This image was taken at an angle; the lesion involves the leg: 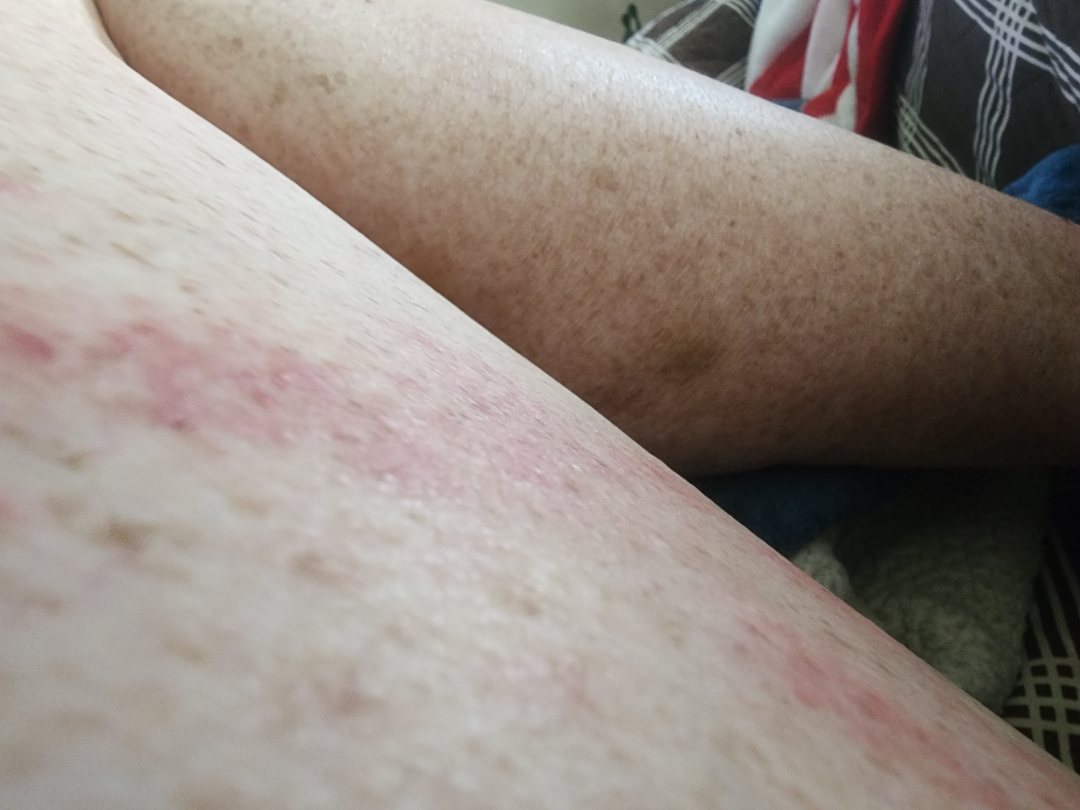Findings:
The reviewer was unable to grade this case for skin condition.